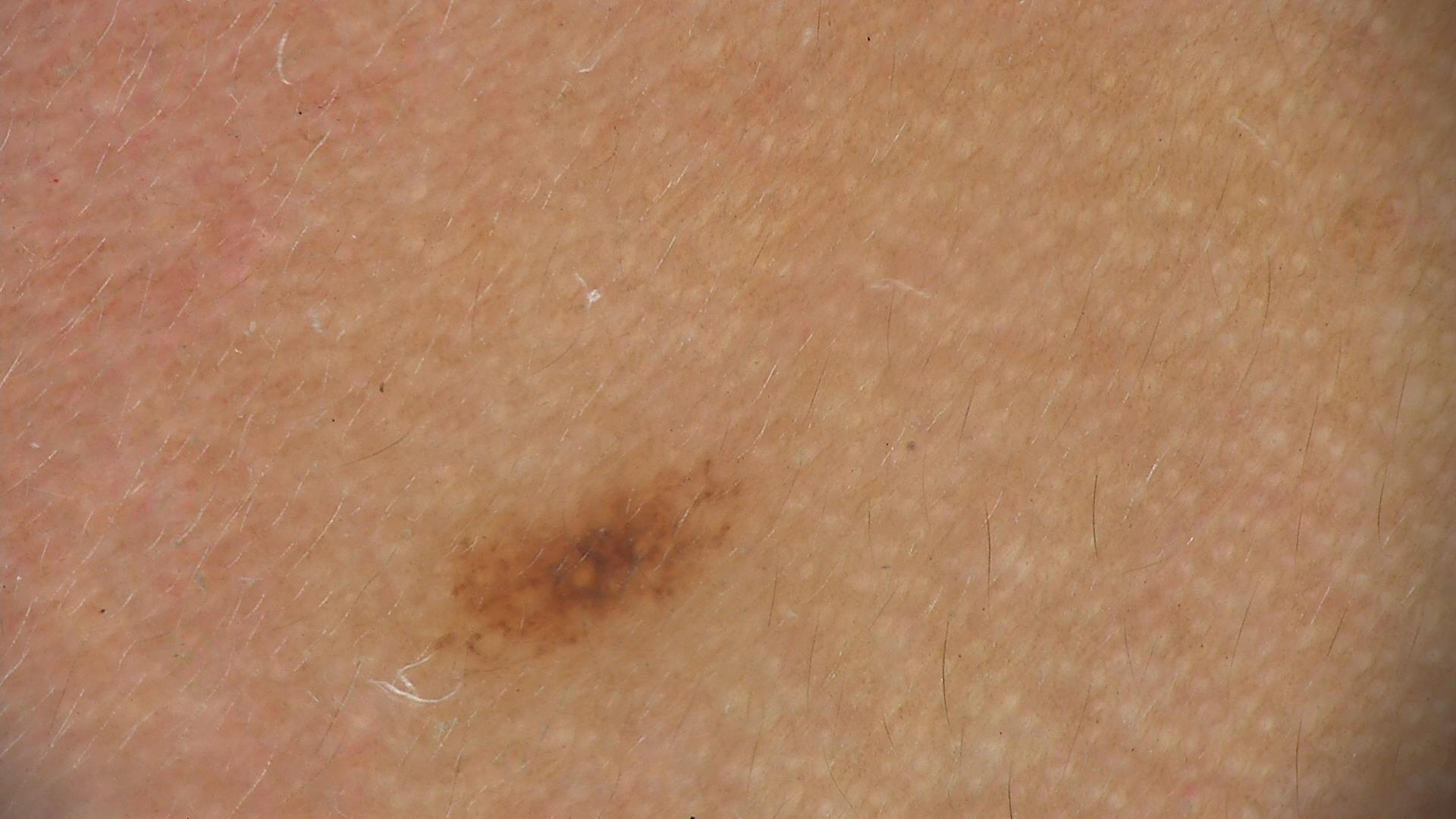A dermoscopic image of a skin lesion. The morphology is that of a compound, banal lesion. The diagnostic label was a Miescher nevus.